A dermoscopic view of a skin lesion.
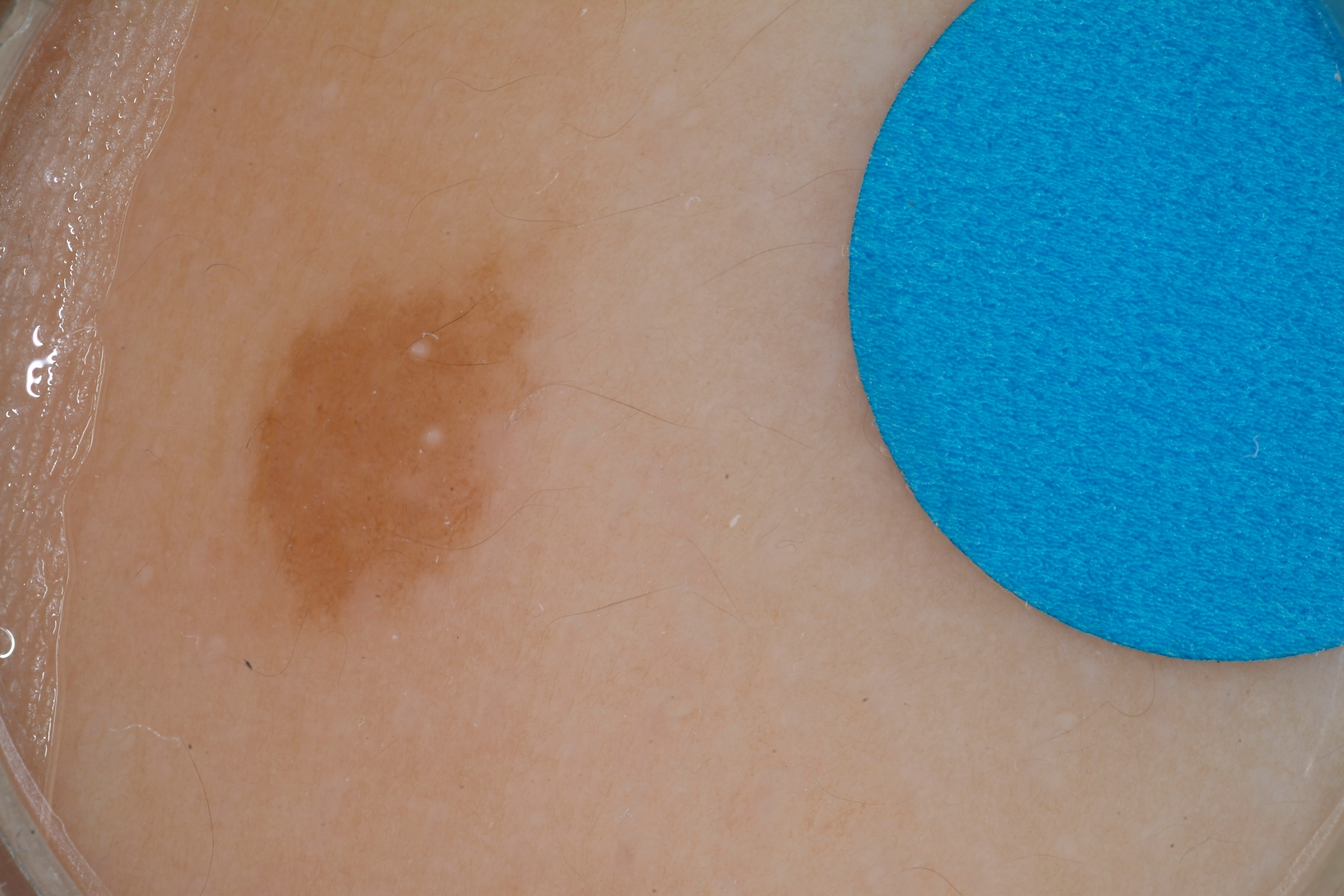Findings: Dermoscopic assessment notes pigment network and milia-like cysts, with no globules, negative network, or streaks. As (left, top, right, bottom), the lesion's extent is bbox=[223, 231, 549, 646]. Impression: The lesion was assessed as a melanocytic nevus.